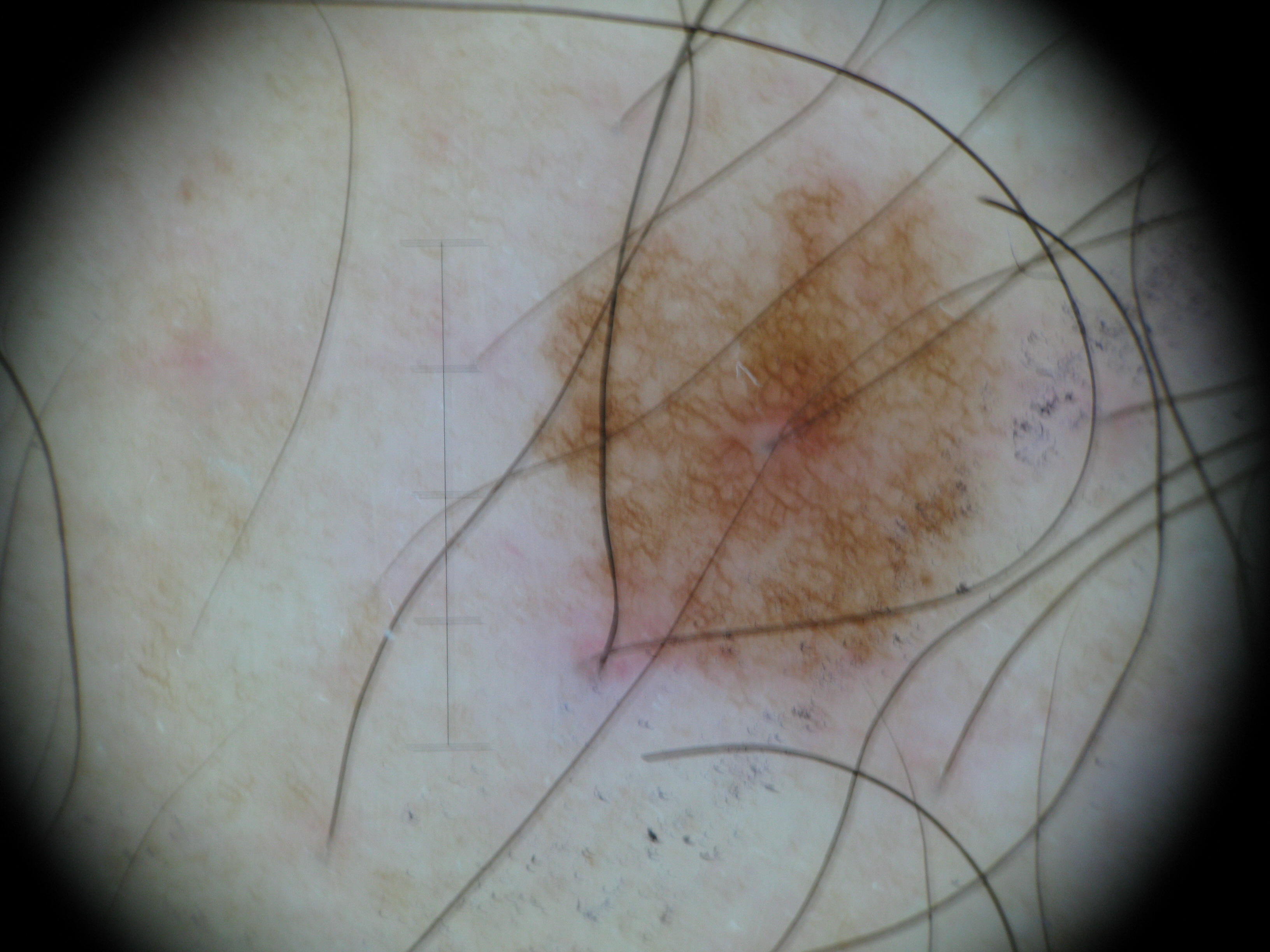• diagnosis · junctional nevus (expert consensus)